The chart records no previous melanoma and no melanoma in first-degree relatives. A female patient aged approximately 50. The patient is Fitzpatrick skin type II. Contact-polarized dermoscopy of a skin lesion.
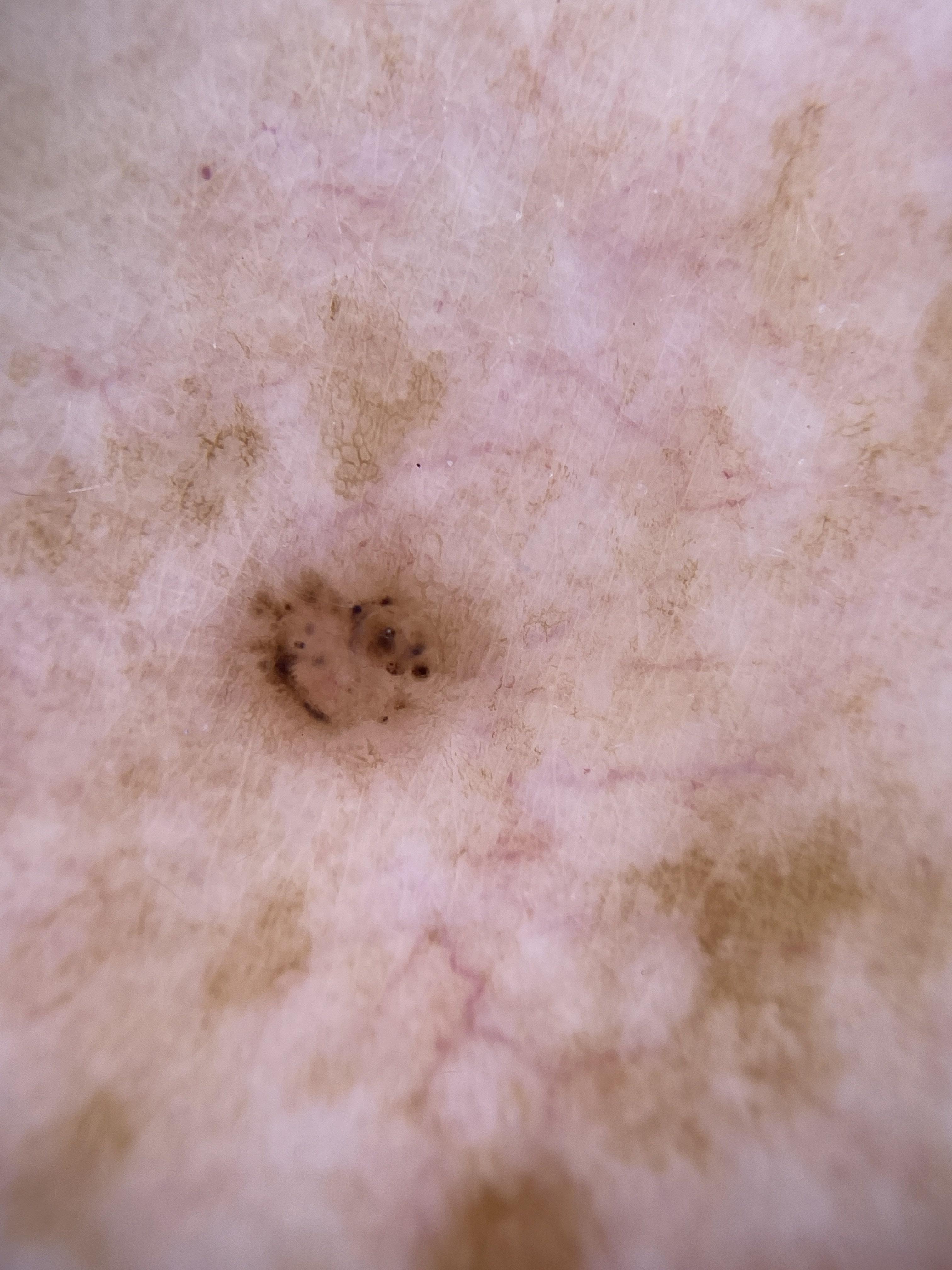The lesion is located on the trunk. The biopsy diagnosis was a basal cell carcinoma.